A dermoscopic view of a skin lesion · a male subject, approximately 70 years of age — 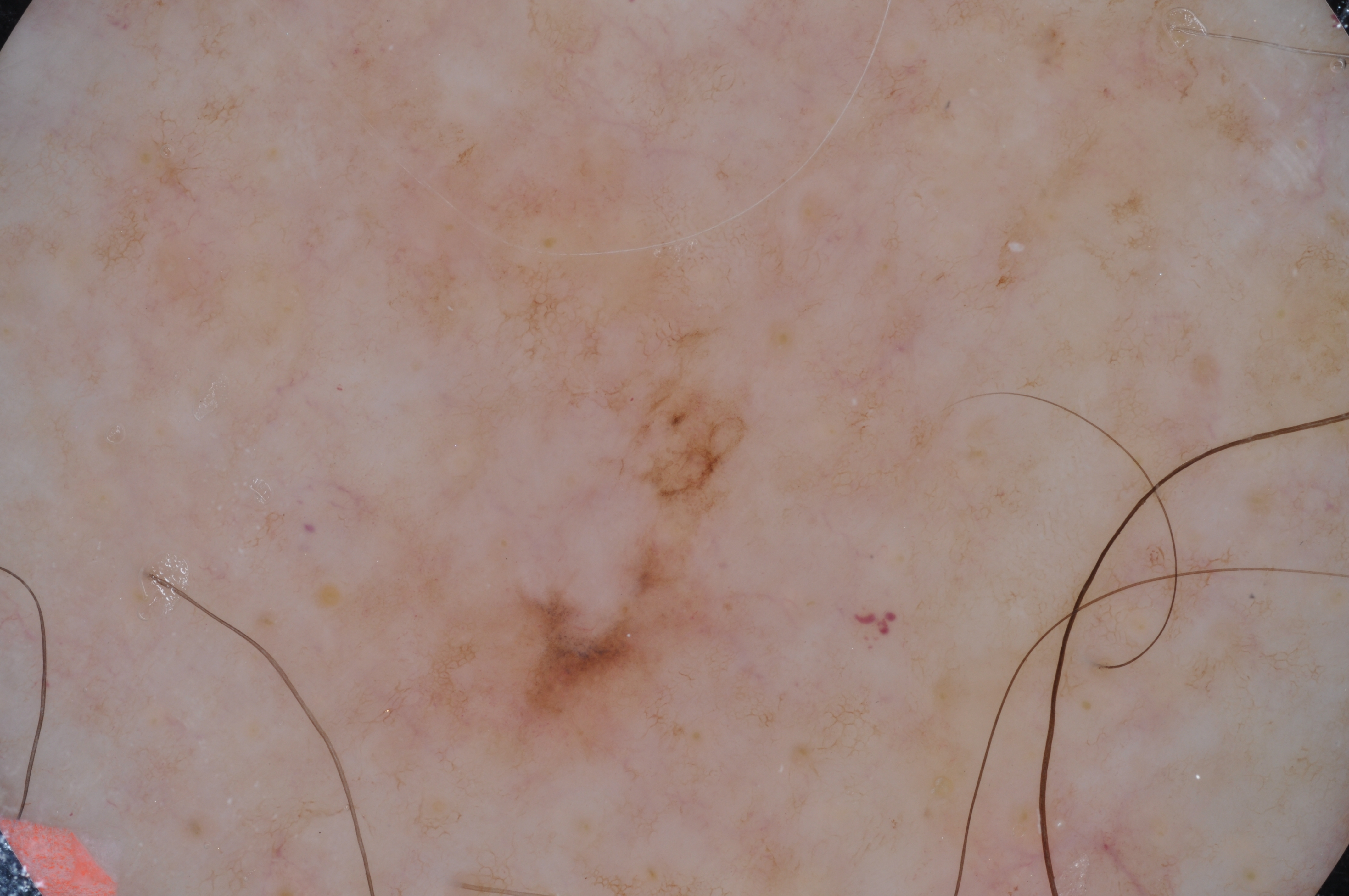| field | value |
|---|---|
| size | ~12% of the field |
| location | left=334, top=311, right=765, bottom=795 |
| dermoscopic findings | pigment network and milia-like cysts |
| diagnosis | a melanoma, a malignant lesion |